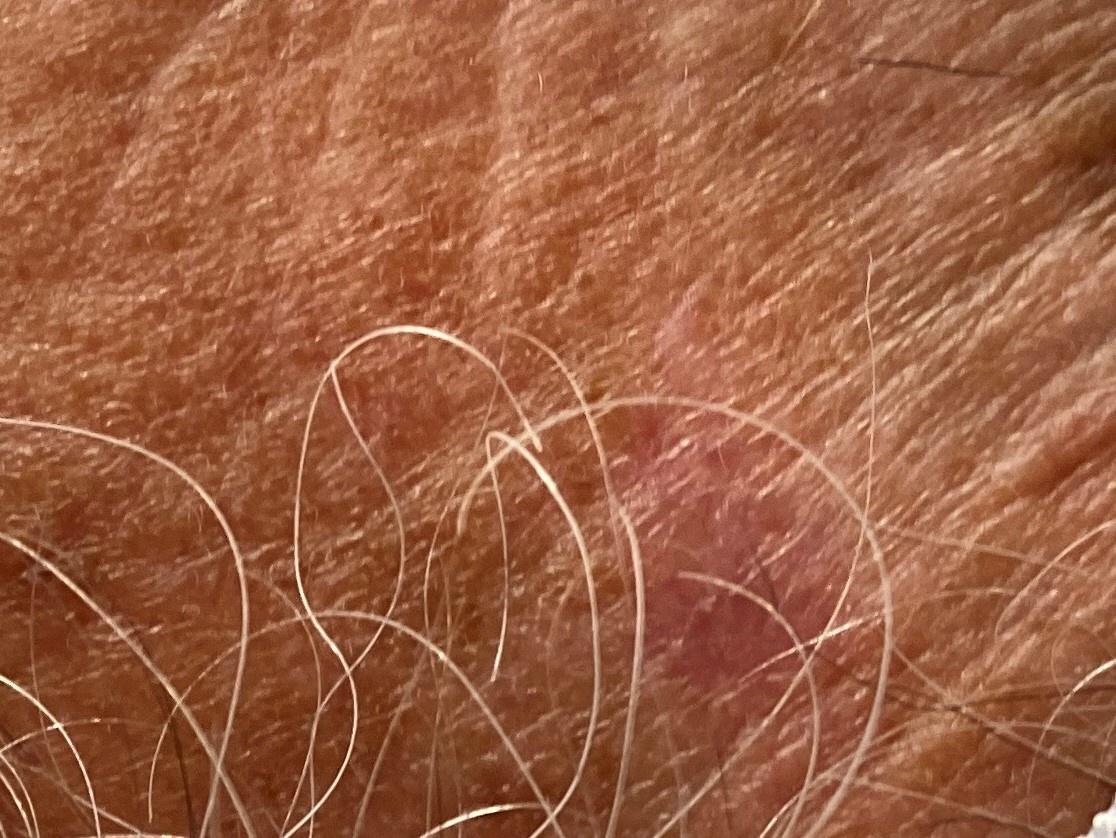Summary:
A clinical photograph showing a skin lesion in context. A male patient in their 70s. The lesion was found on the head or neck.
Pathology:
Biopsy-confirmed as a basal cell carcinoma.